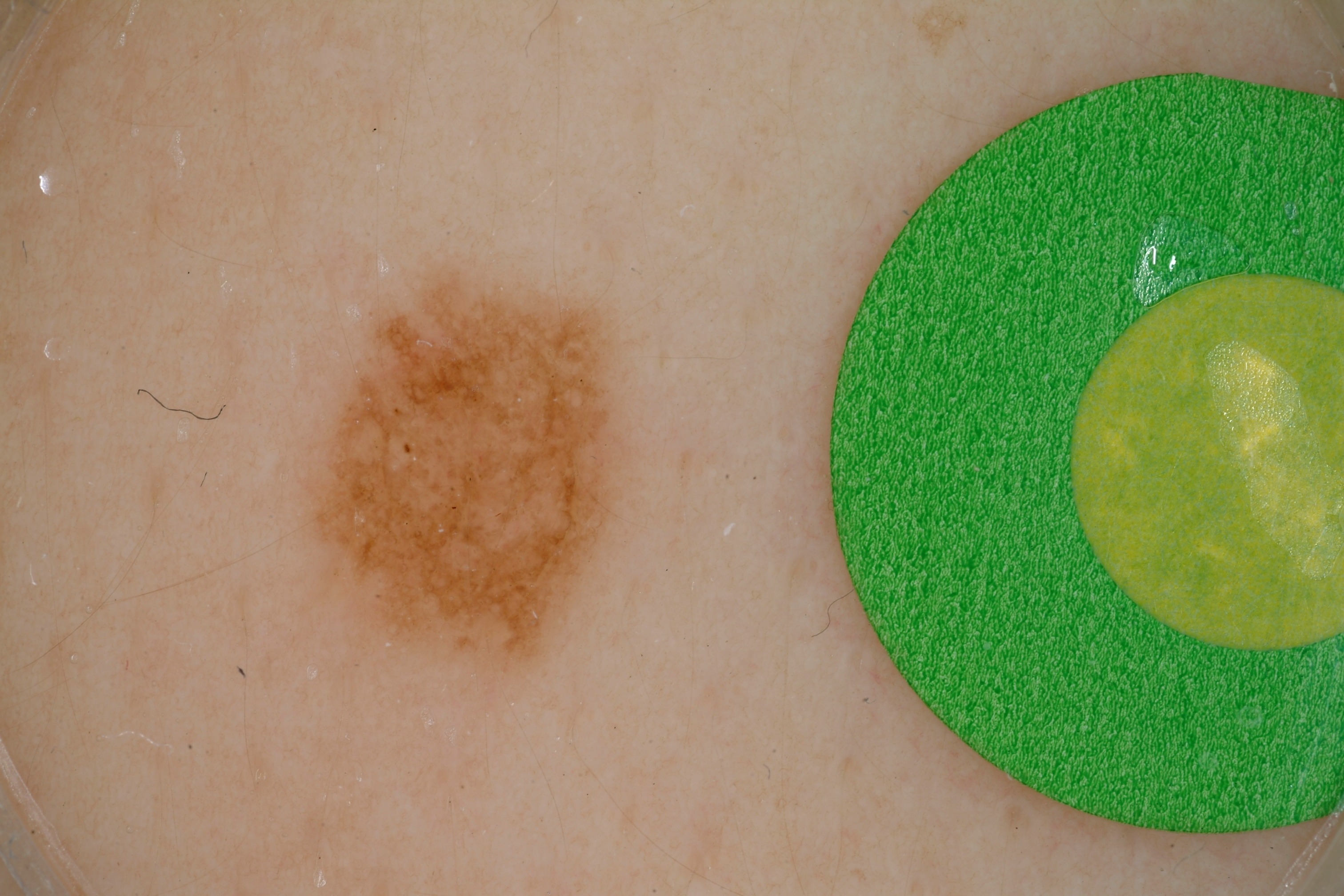Q: What are the patient's age and sex?
A: female, aged approximately 15
Q: What is the imaging modality?
A: dermoscopy of a skin lesion
Q: What does dermoscopy show?
A: pigment network; absent: streaks, negative network, and milia-like cysts
Q: Where is the lesion in the image?
A: x1=282, y1=243, x2=651, y2=684
Q: Lesion extent?
A: ~10% of the field
Q: What did the assessment conclude?
A: a melanocytic nevus